A close-up photograph: 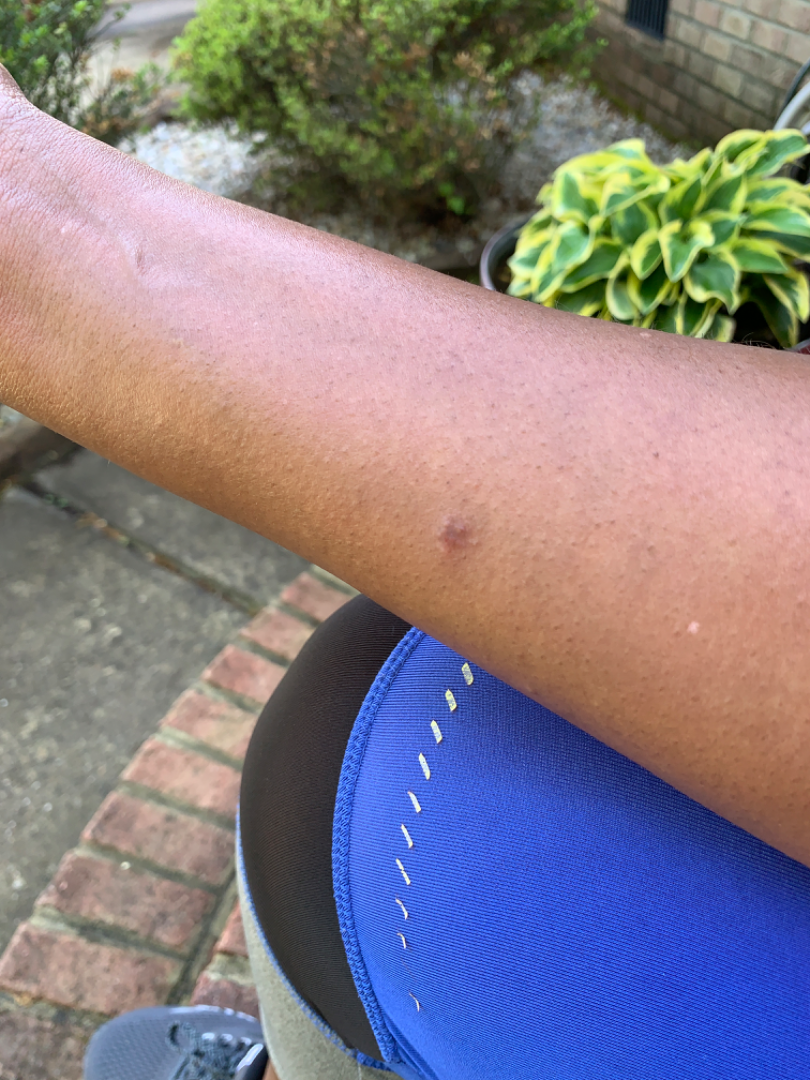Impression:
The reviewer was unable to grade this case for skin condition.